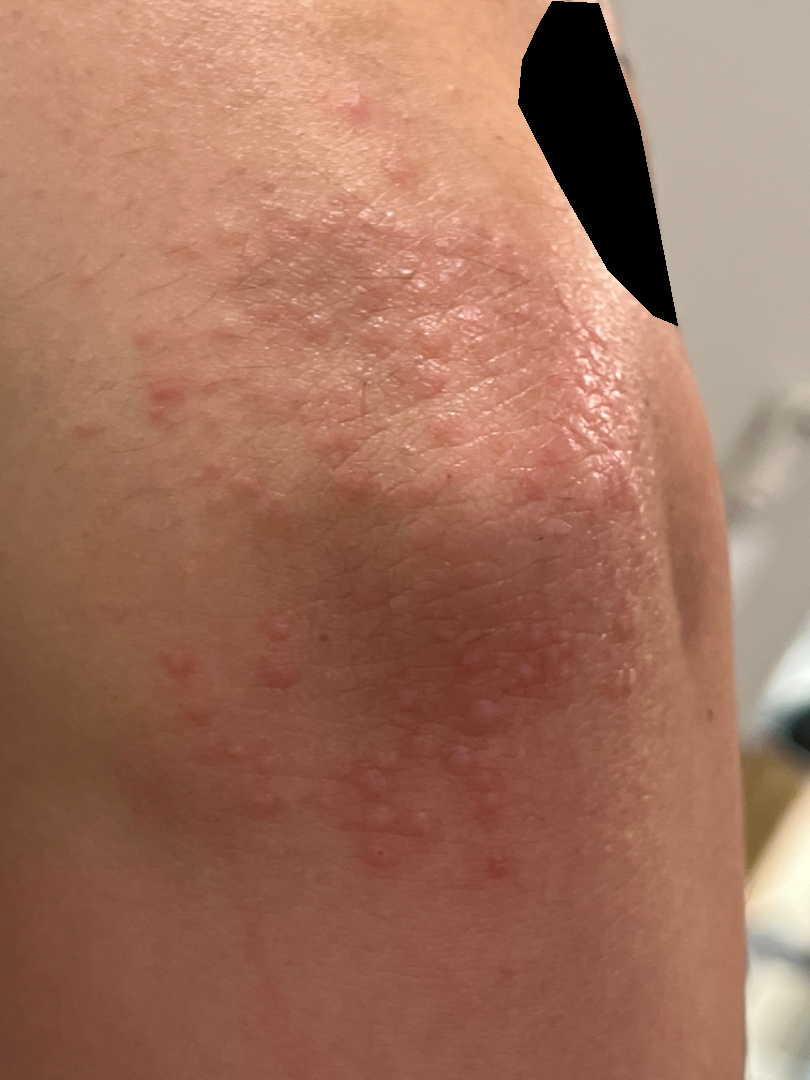Notes:
– patient — female
– image framing — close-up
– body site — arm
– differential diagnosis — Eczema and Lichen Simplex Chronicus were considered with similar weight; a remote consideration is Psoriasis; less likely is Perforating dermatosis; less probable is Granuloma annulare; a more distant consideration is Dermatitis herpetiformis